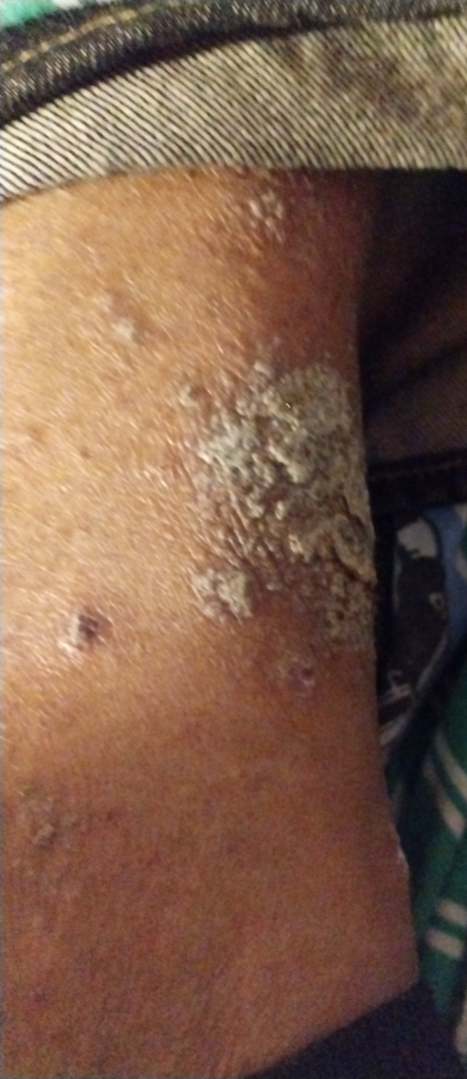Impression:
On photographic review, most consistent with Psoriasis.